The lesion involves the head or neck · the patient is a female aged 18–29 · the photograph is a close-up of the affected area: 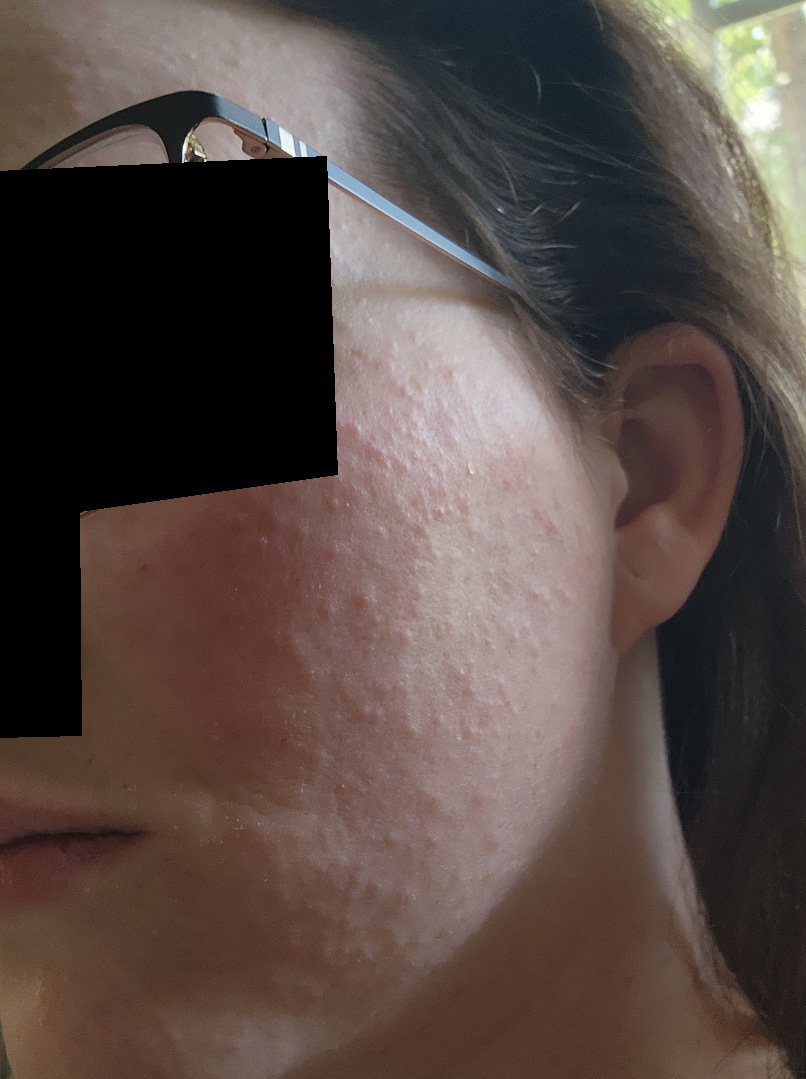The lesion is associated with enlargement.
Present for one to four weeks.
Skin tone: Fitzpatrick II.
Texture is reported as raised or bumpy.
The patient described the issue as a rash.
Three dermatologists independently reviewed the case: most consistent with Rosacea; an alternative is Allergic Contact Dermatitis; lower on the differential is Acne; less probable is Miliaria; less likely is Folliculitis.